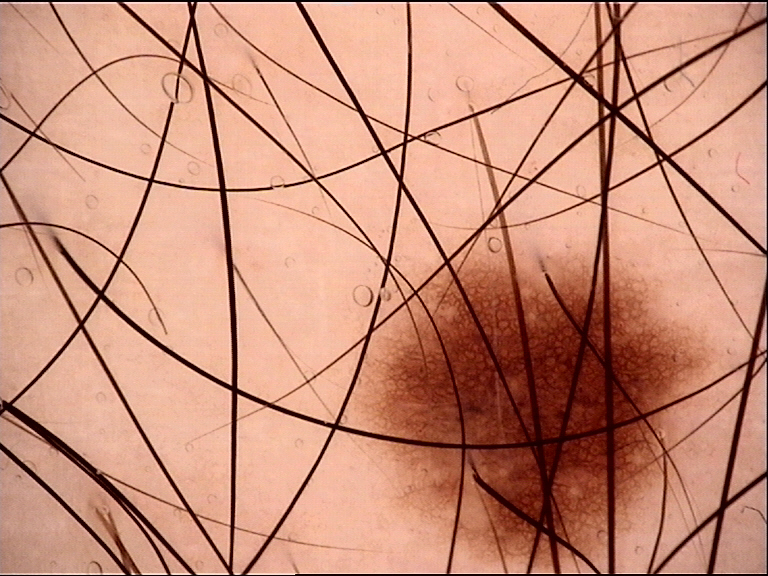Case:
A dermatoscopic image of a skin lesion.
Impression:
Consistent with a banal lesion — a junctional nevus.